The condition has been present for one to four weeks · the patient described the issue as a rash · located on the front of the torso · the lesion is associated with enlargement, pain, burning, itching and bothersome appearance · an image taken at a distance · FST II; non-clinician graders estimated 2 on the Monk Skin Tone · the patient reports the lesion is rough or flaky and raised or bumpy.
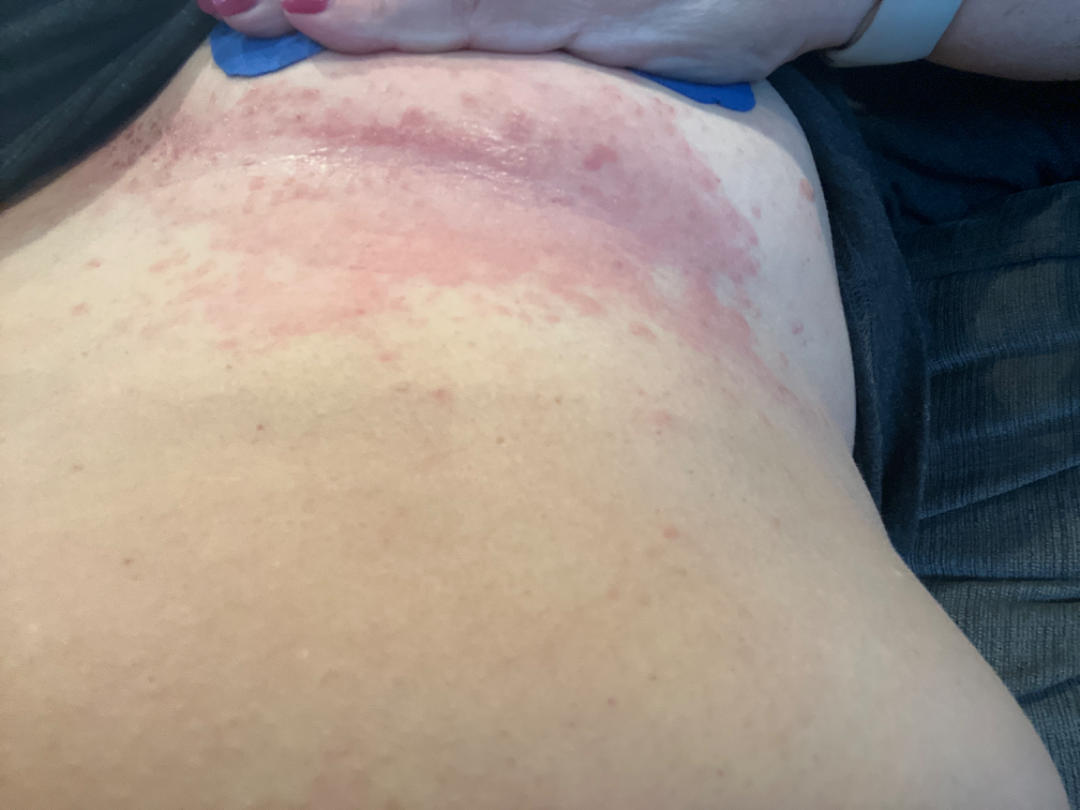differential:
  leading:
    - Candida intertrigo
  considered:
    - Allergic Contact Dermatitis
  unlikely:
    - Psoriasis